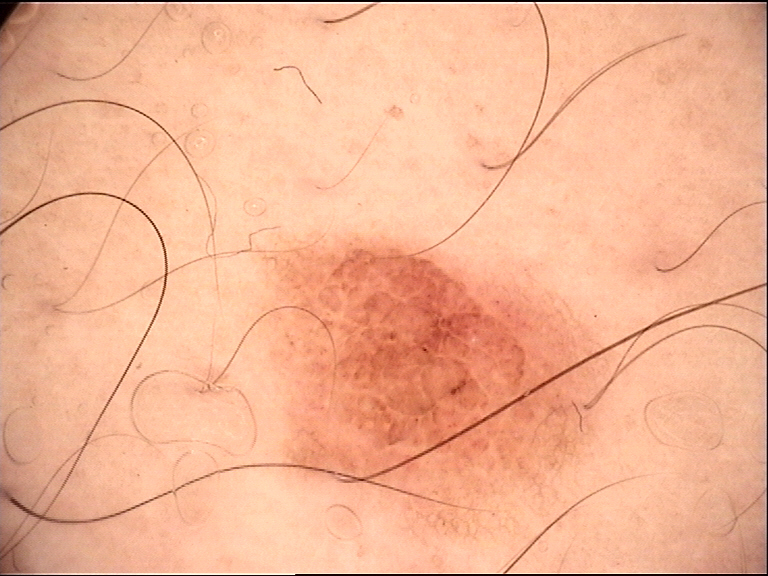The diagnostic label was a dysplastic compound nevus.